An image taken at a distance; the affected area is the arm.
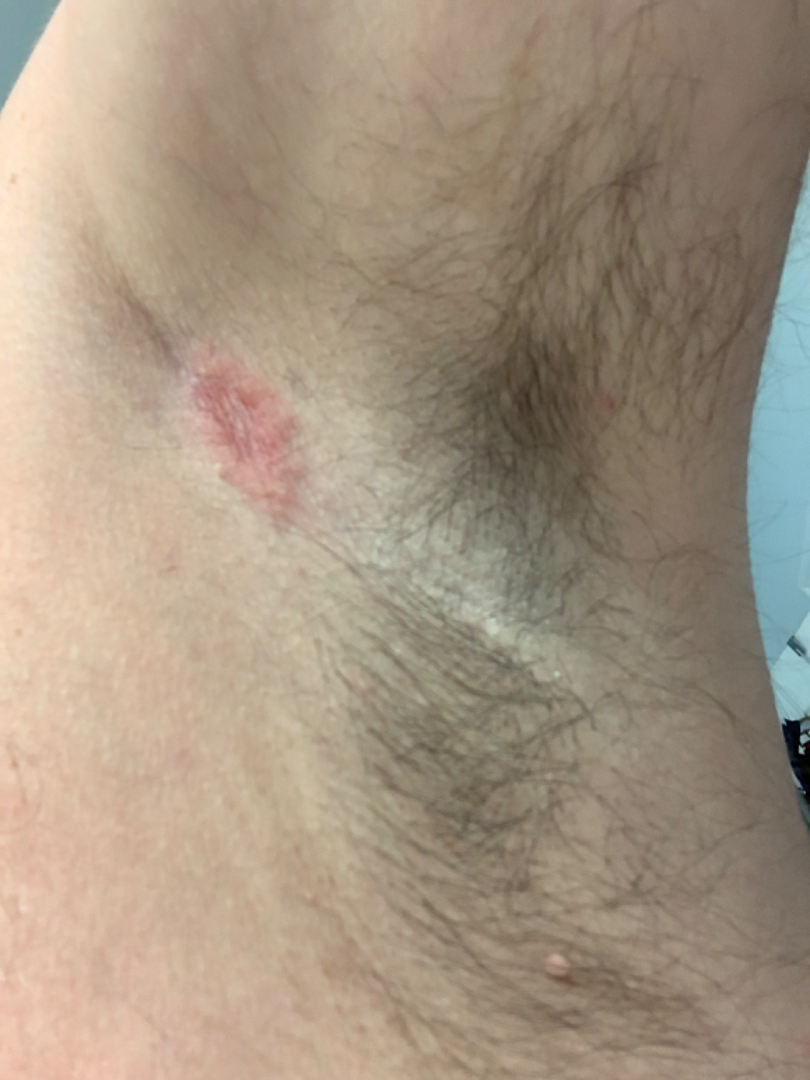Notes:
– assessment: could not be assessed